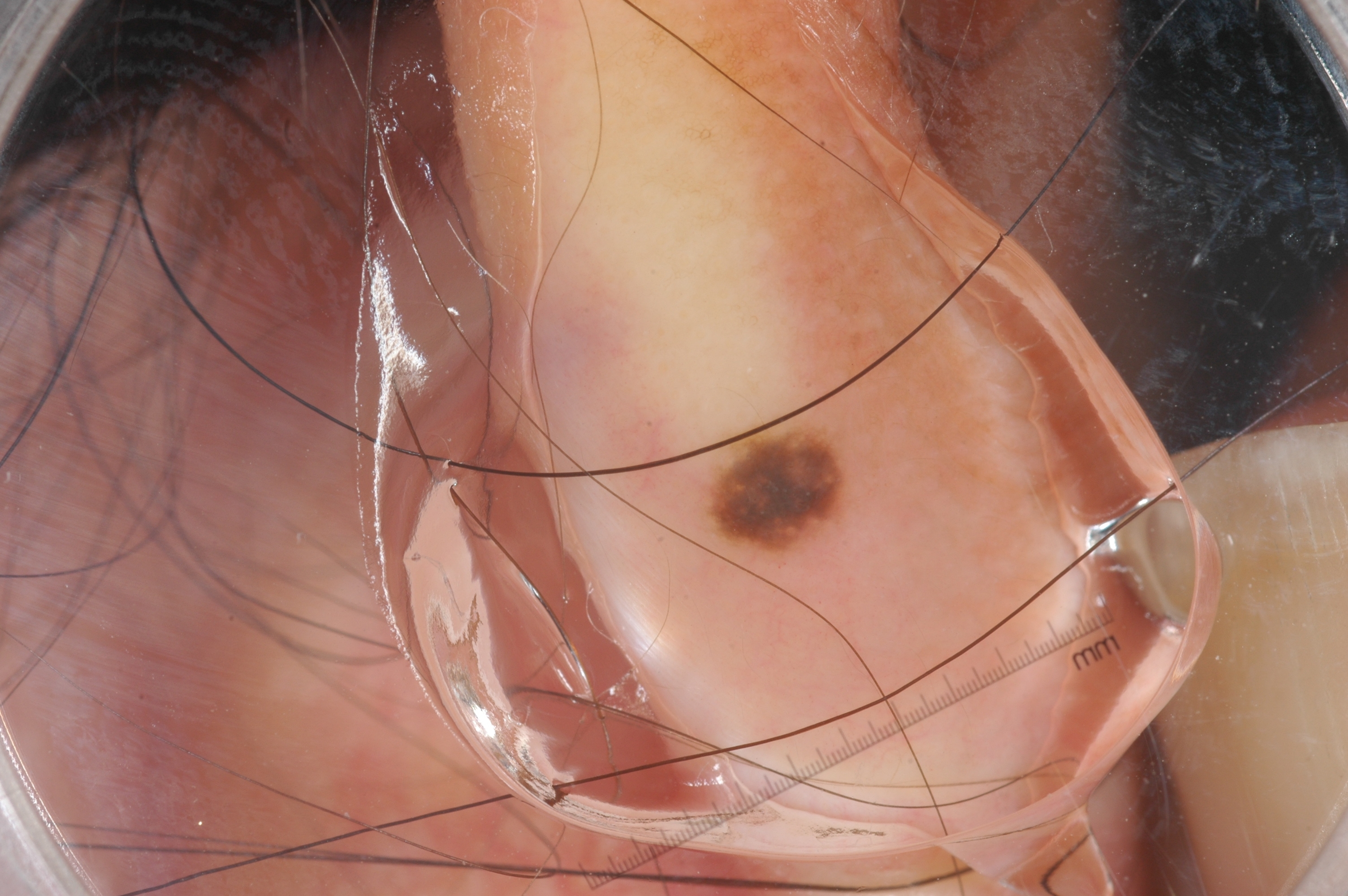imaging = dermoscopy of a skin lesion | size = ~1% of the field | absent dermoscopic features = negative network, streaks, pigment network, and milia-like cysts | lesion bbox = <box>707, 429, 855, 562</box> | diagnostic label = a melanocytic nevus.